The patient is a male in their 50s; a dermoscopic close-up of a skin lesion — 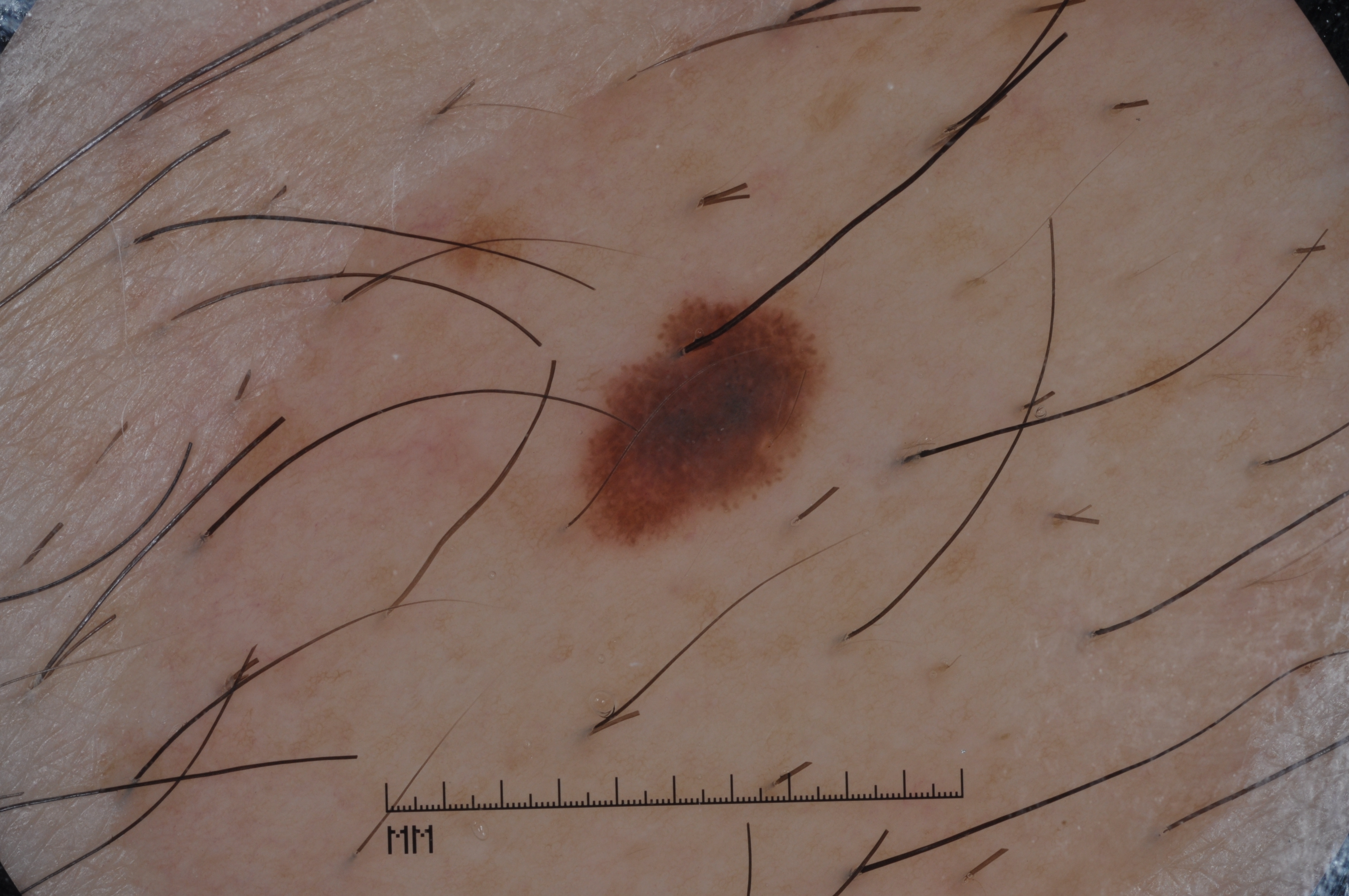dermoscopic features — streaks and pigment network; absent: milia-like cysts and negative network | location — [590, 294, 822, 539] | assessment — a melanoma.